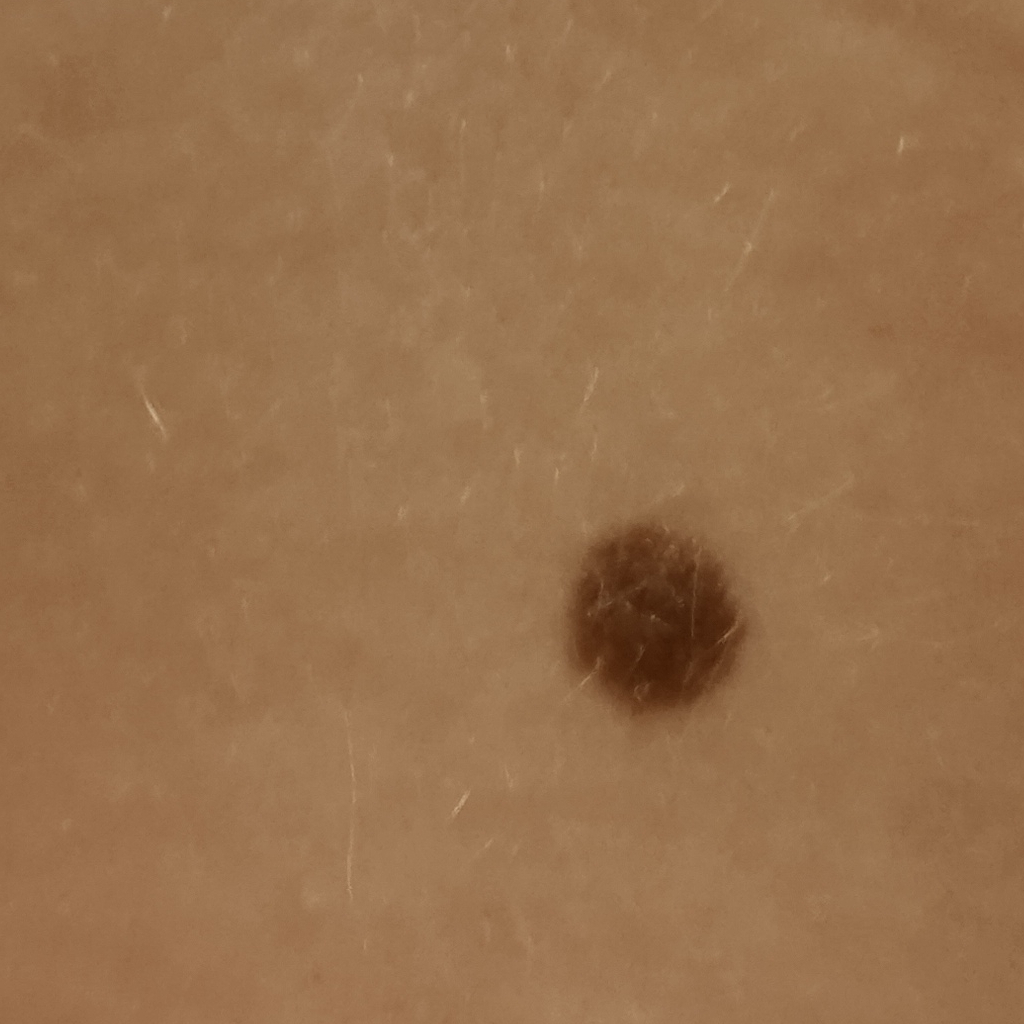Findings: Imaged for a research study, with no referral diagnosis recorded. A female subject 26 years of age. The lesion involves the back. Impression: The dermatologists' assessment was a melanocytic nevus.